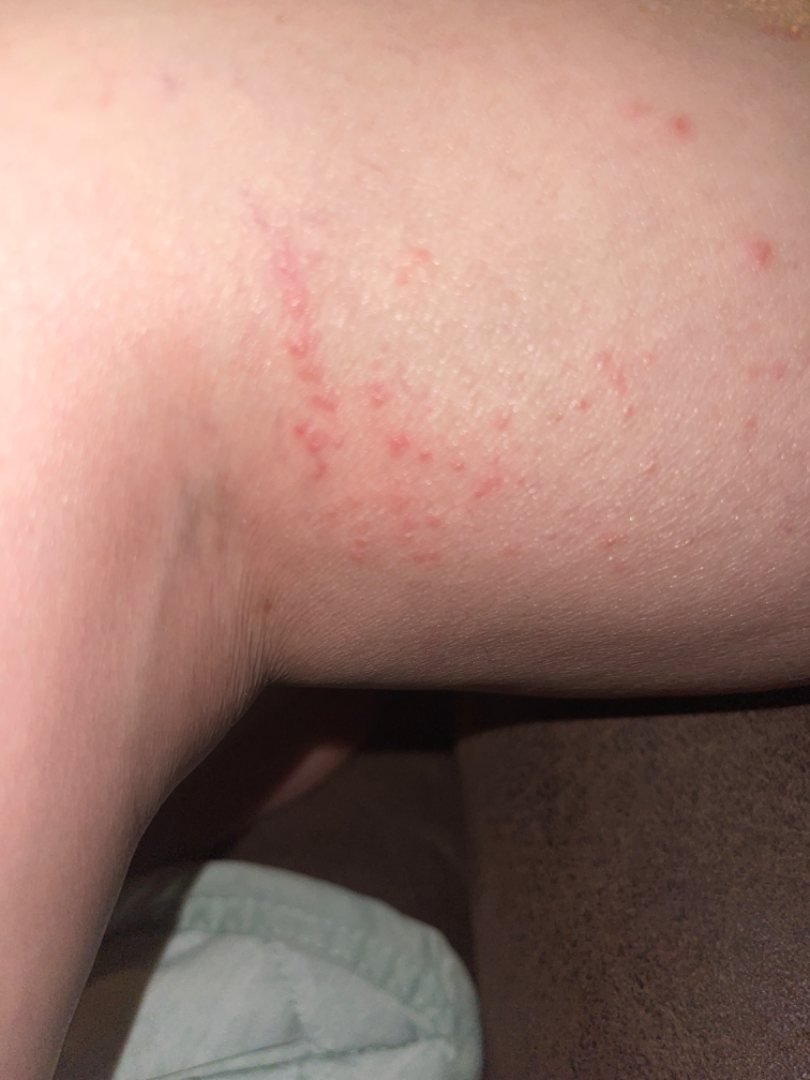<summary>
<assessment>could not be assessed</assessment>
<systemic_symptoms>none reported</systemic_symptoms>
<body_site>leg</body_site>
<shot_type>at an angle</shot_type>
<patient_category>a rash</patient_category>
<patient>female, age 40–49</patient>
<symptoms>none reported</symptoms>
<duration>less than one week</duration>
</summary>